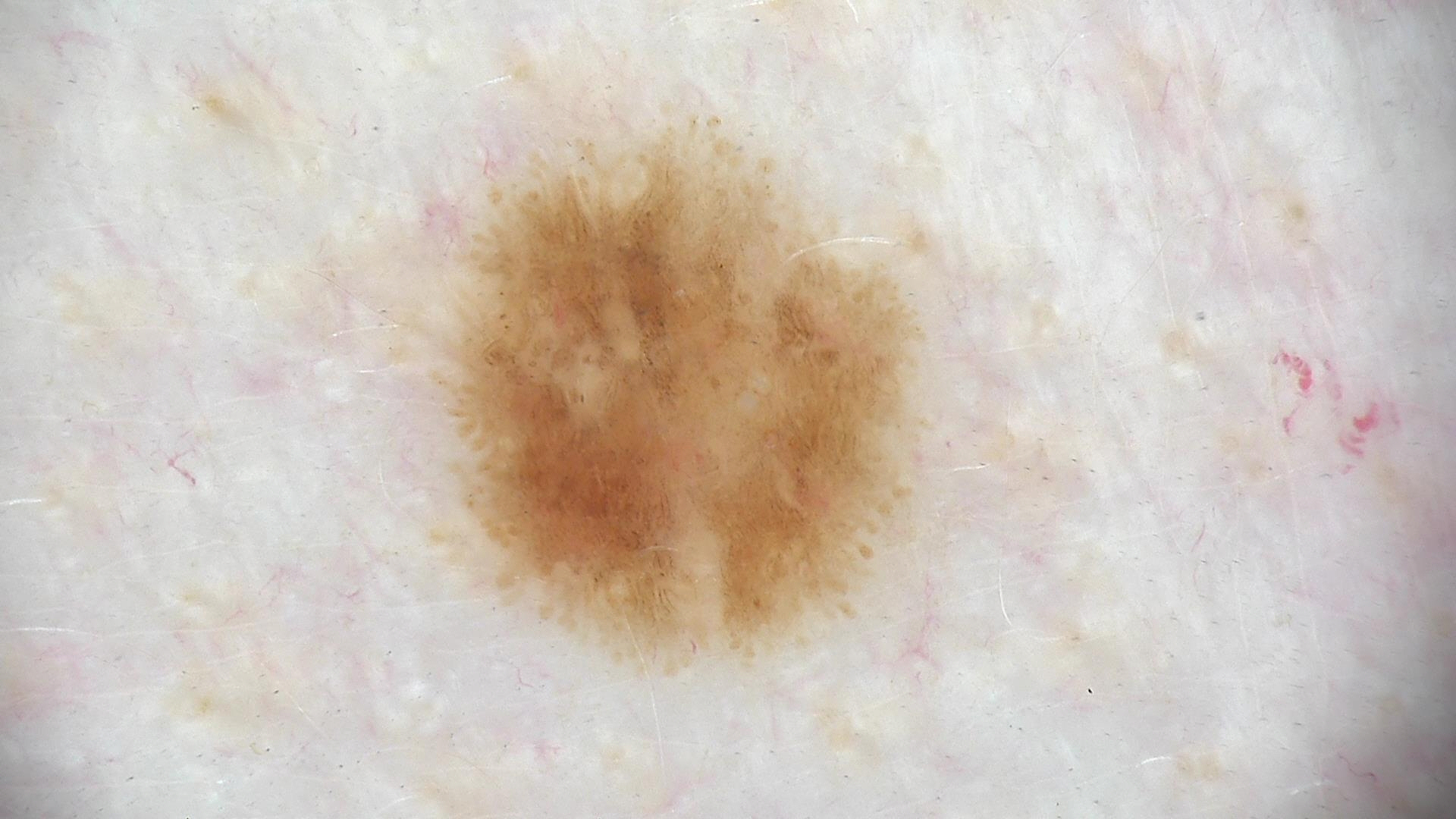modality=dermatoscopy
assessment=dysplastic junctional nevus (expert consensus)